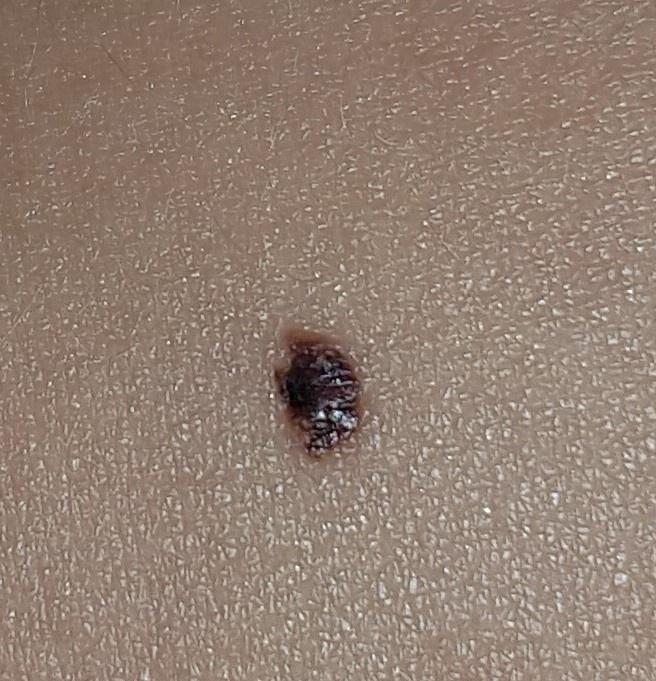Histopathological examination showed a nevus.